A skin lesion imaged with a dermatoscope: 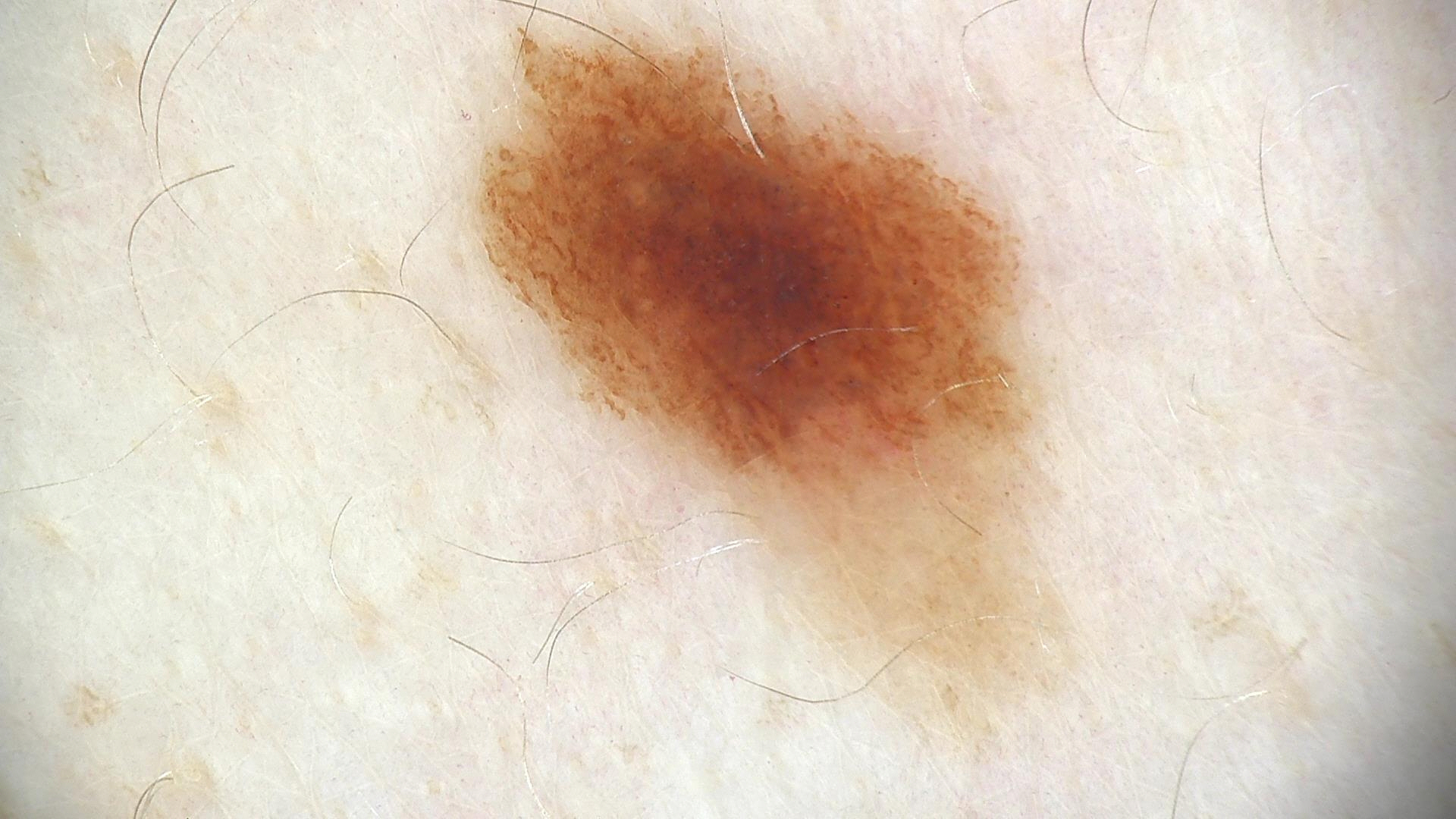{"diagnosis": {"name": "dysplastic junctional nevus", "code": "jd", "malignancy": "benign", "super_class": "melanocytic", "confirmation": "expert consensus"}}